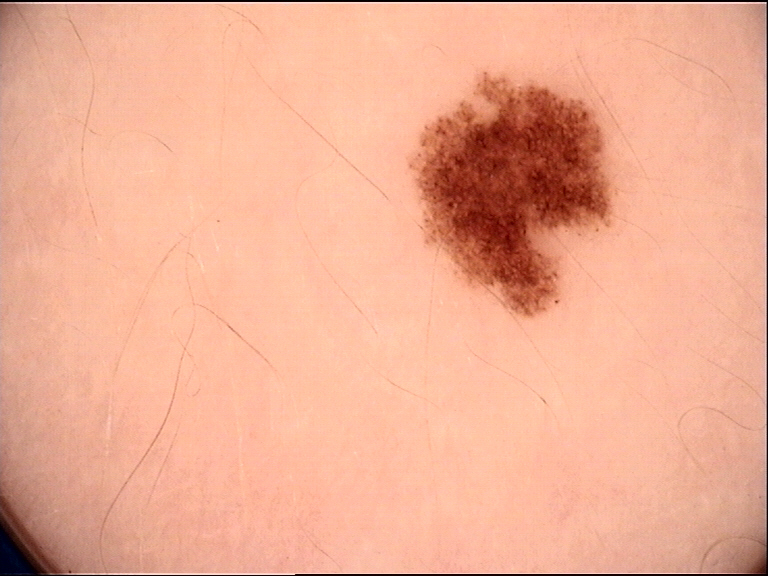{
  "diagnosis": {
    "name": "dysplastic junctional nevus",
    "code": "jd",
    "malignancy": "benign",
    "super_class": "melanocytic",
    "confirmation": "expert consensus"
  }
}